The patient is 40–49, male; located on the back of the torso, arm and leg; the photo was captured at a distance.
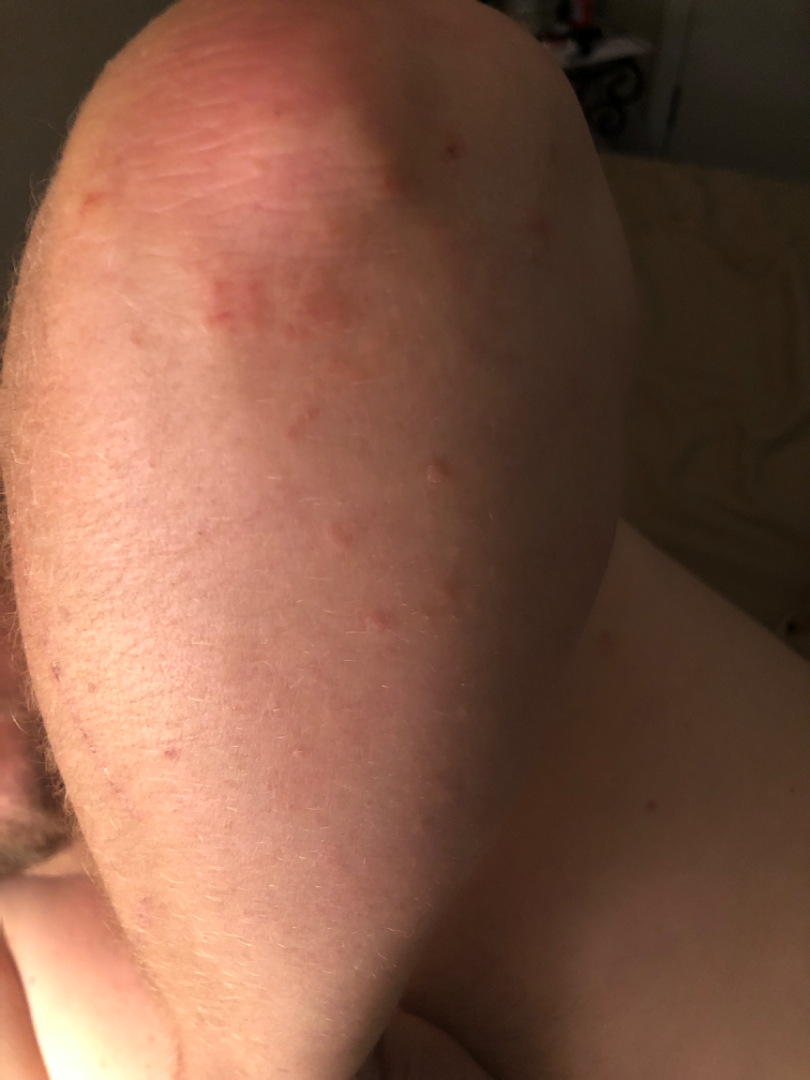Impression:
The case was indeterminate on photographic review.